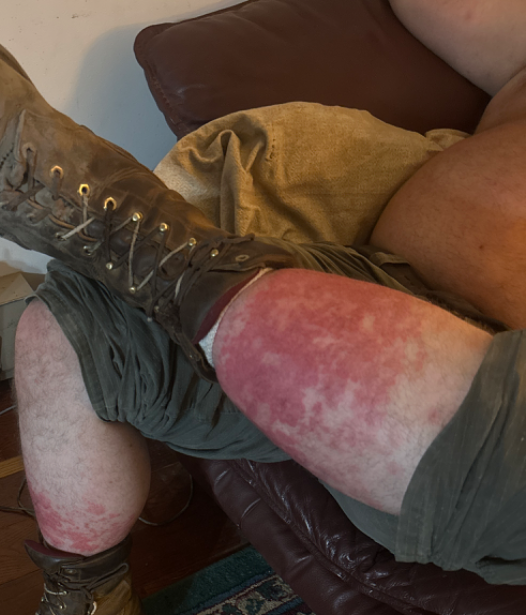Impression: The case was indeterminate on photographic review. History: The patient notes the condition has been present for less than one week. The patient is a male aged 40–49. The patient notes associated fatigue. The lesion involves the leg. The photograph was taken at an angle.